The photograph is a close-up of the affected area:
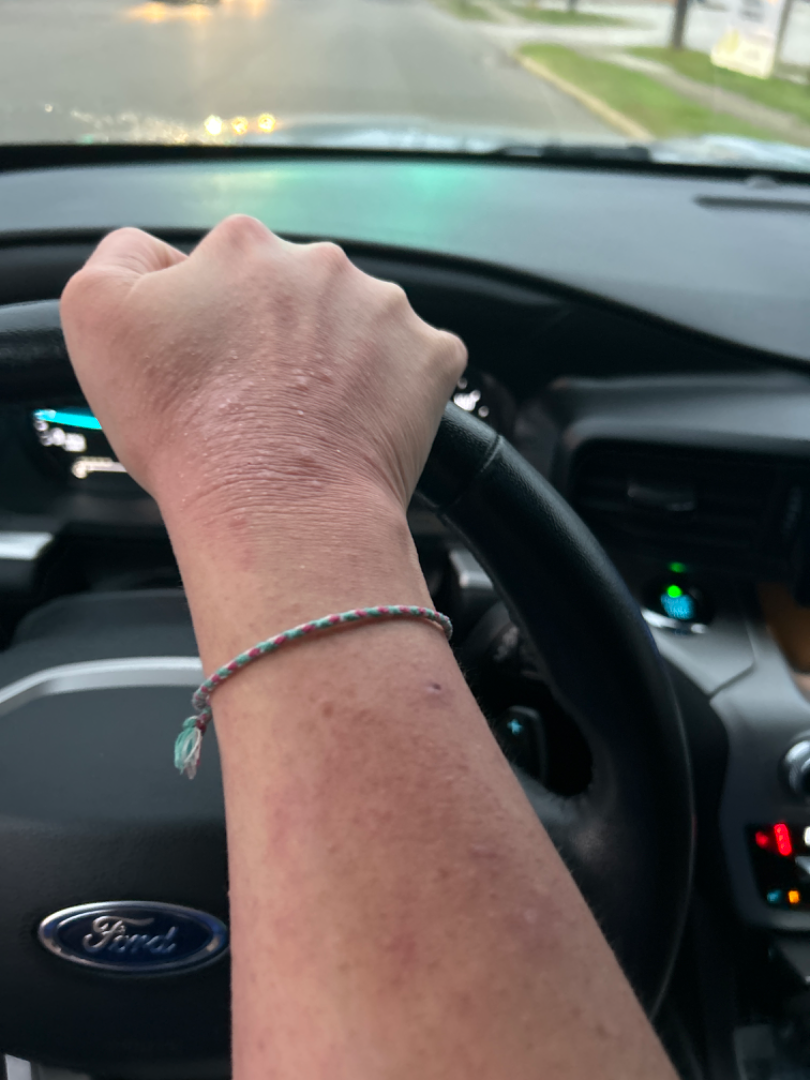Diagnostic features were not clearly distinguishable in this photograph.